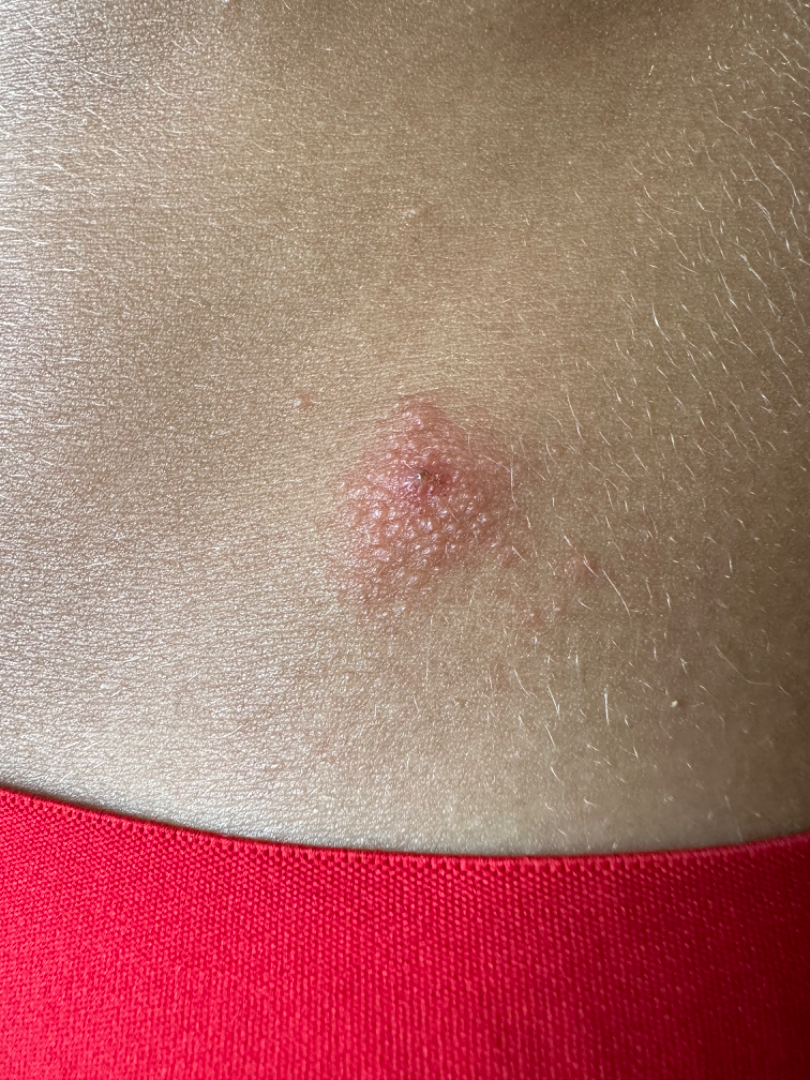The dermatologist could not determine a likely condition from the photograph alone.
This is a close-up image.
Located on the front of the torso.